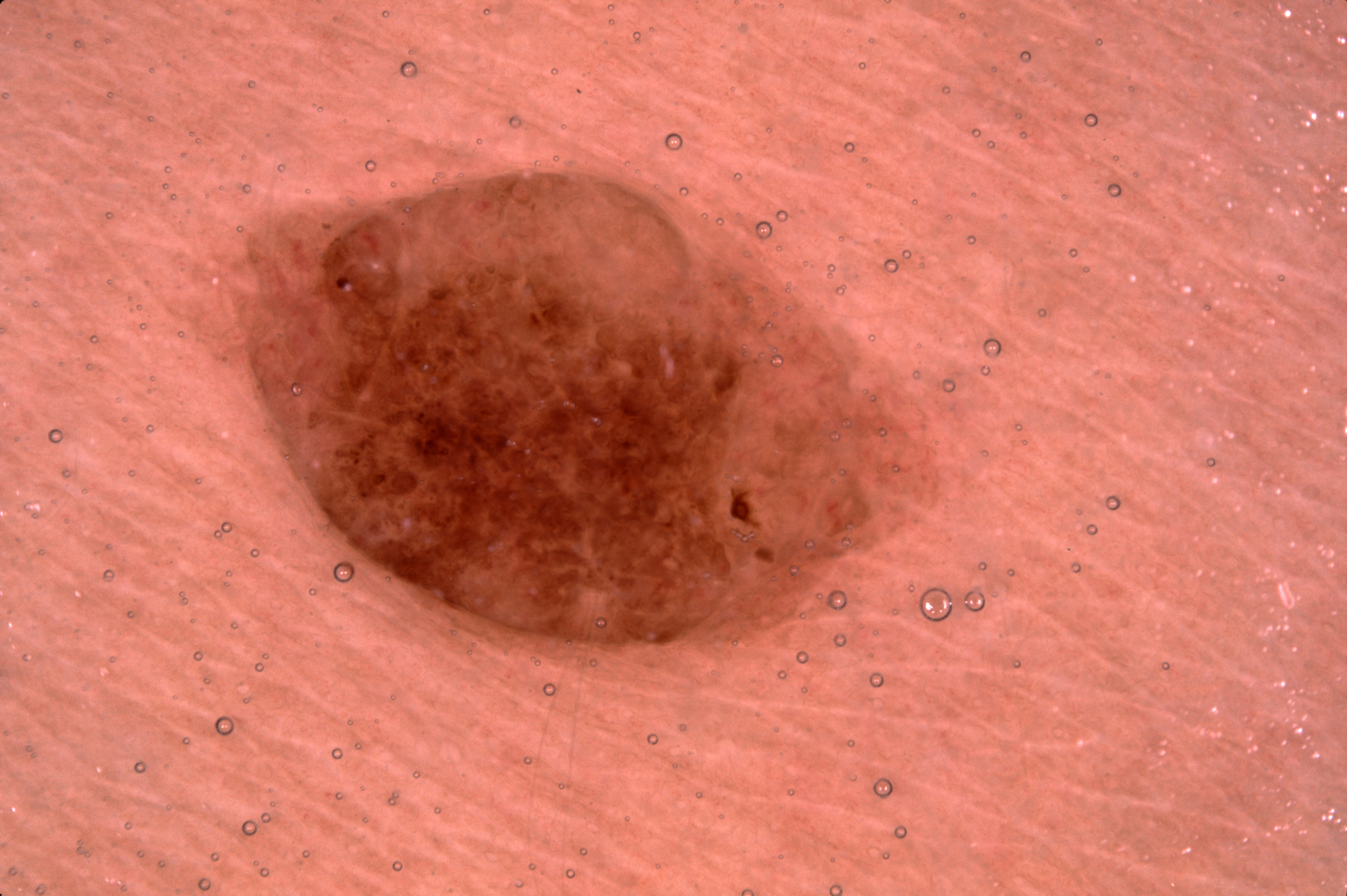The patient is a female aged 13 to 17. A dermatoscopic image of a skin lesion. Dermoscopic review identifies no pigment network, streaks, milia-like cysts, or negative network. As (left, top, right, bottom), the lesion is located at (164, 160, 949, 722). A mid-sized lesion within the field. The lesion was assessed as a melanocytic nevus.